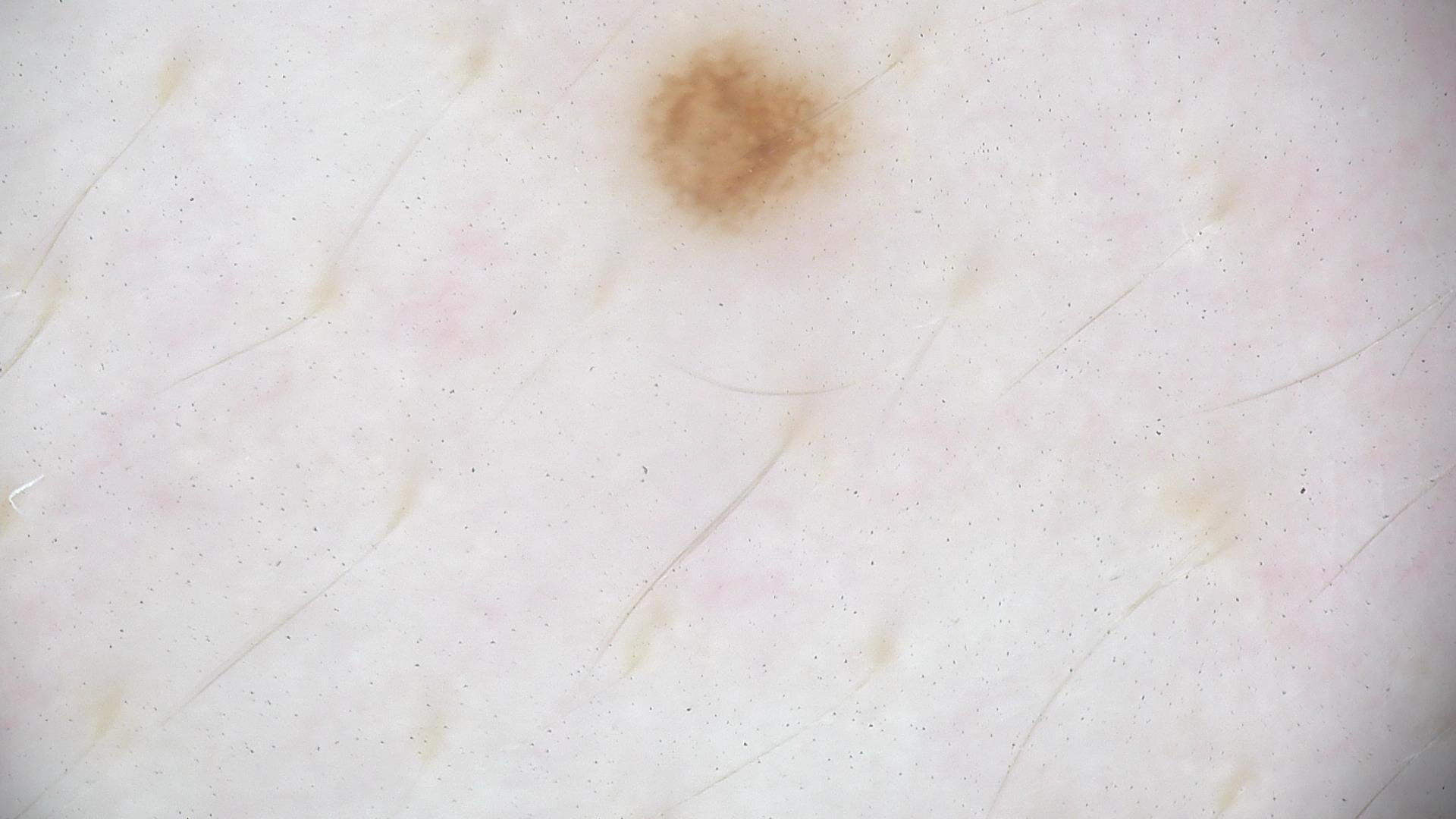A skin lesion imaged with a dermatoscope. Consistent with a dysplastic junctional nevus.